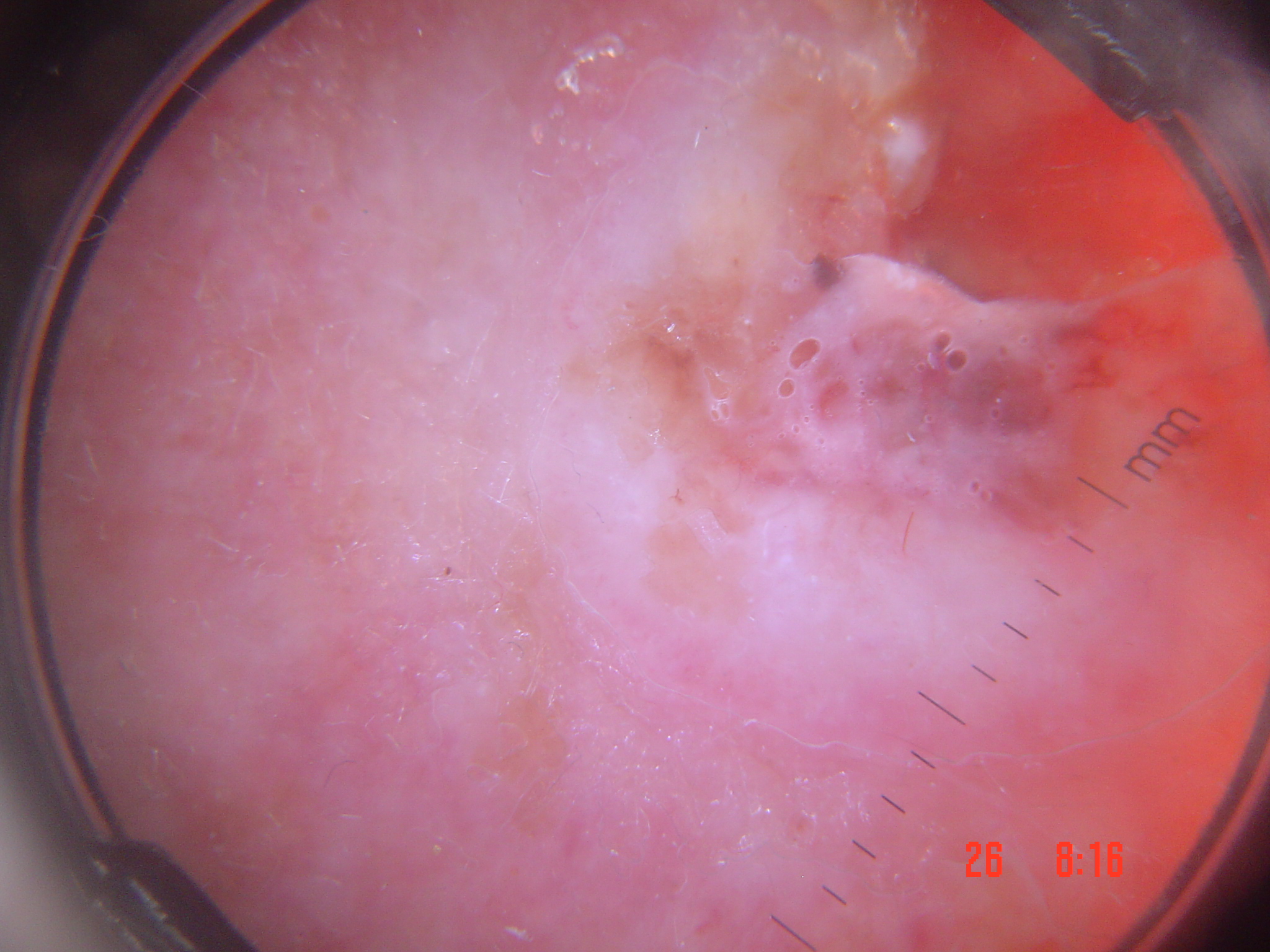Findings:
A skin lesion imaged with a dermatoscope. The morphology is that of a keratinocytic lesion.
Conclusion:
The biopsy diagnosis was a squamous cell carcinoma.